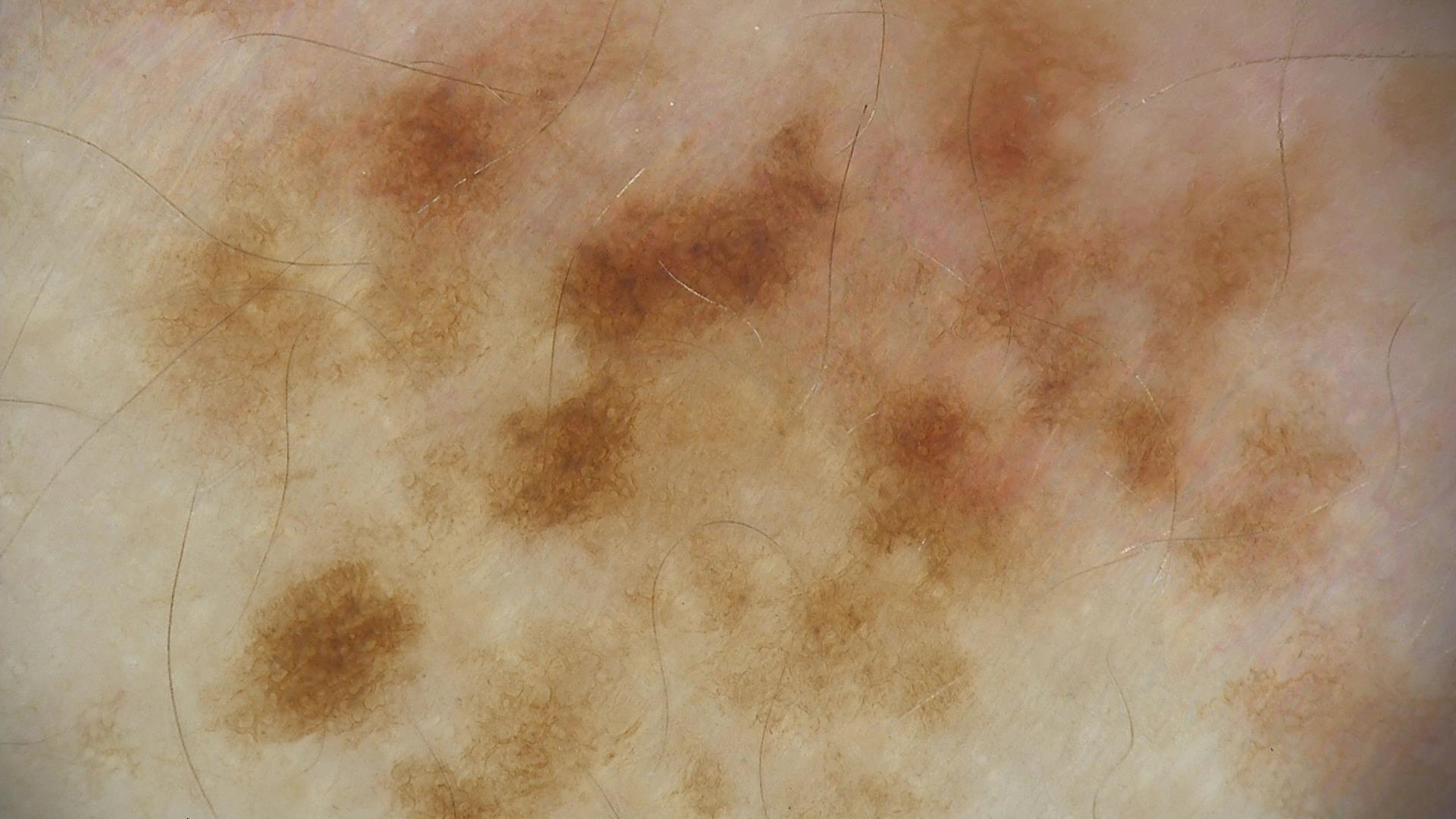assessment = dysplastic junctional nevus (expert consensus)